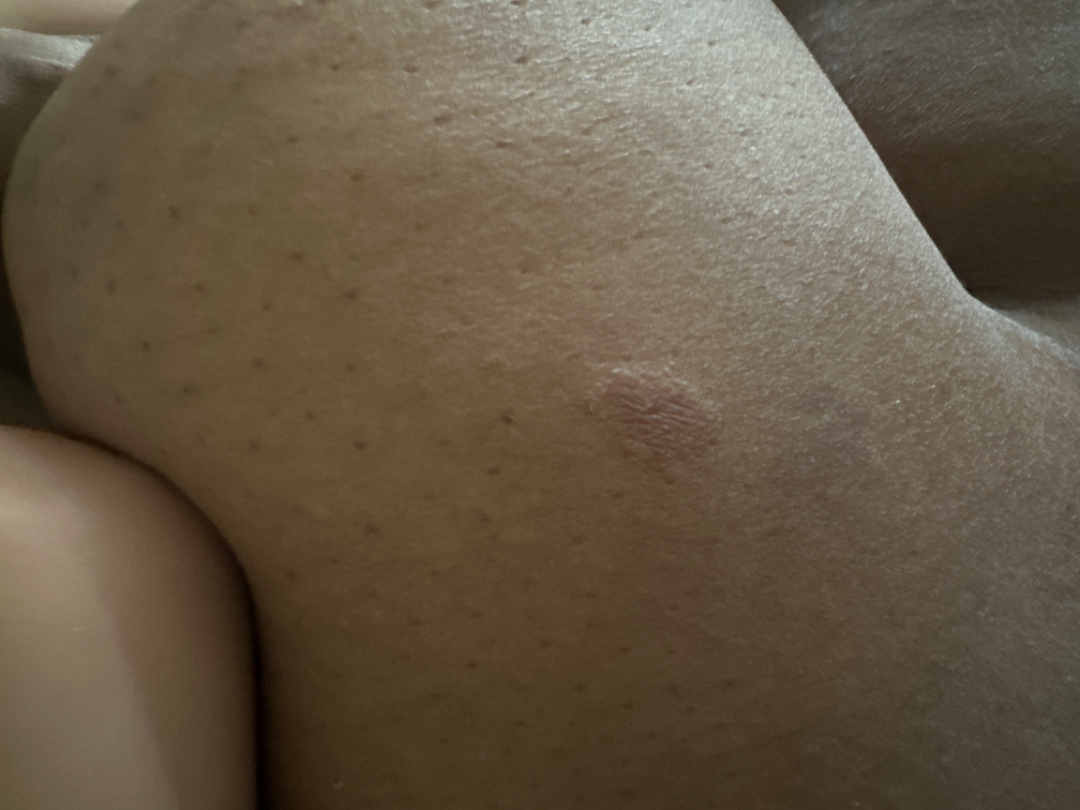{
  "assessment": "ungradable on photographic review",
  "shot_type": "at a distance"
}